The affected area is the leg, front of the torso and arm; the contributor is a female aged 30–39; this is a close-up image:
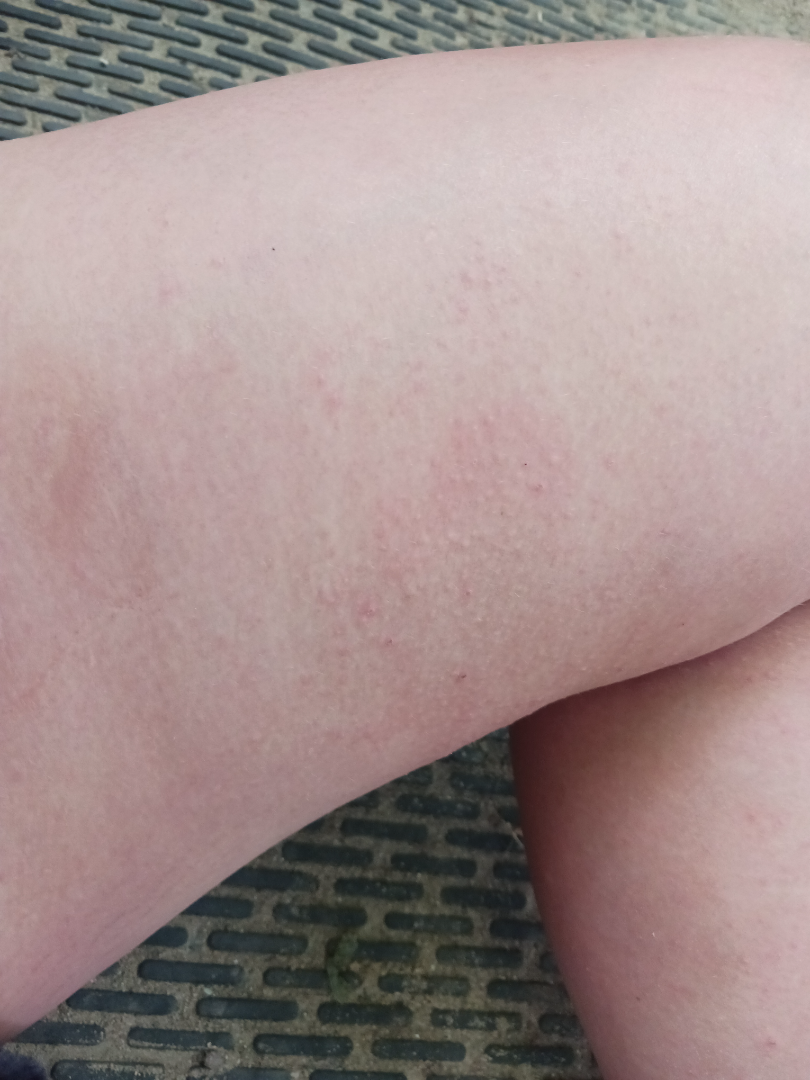Review:
The reviewing clinician's impression was: consistent with Acute and chronic dermatitis.